A male subject, in their 40s. A dermoscopic view of a skin lesion.
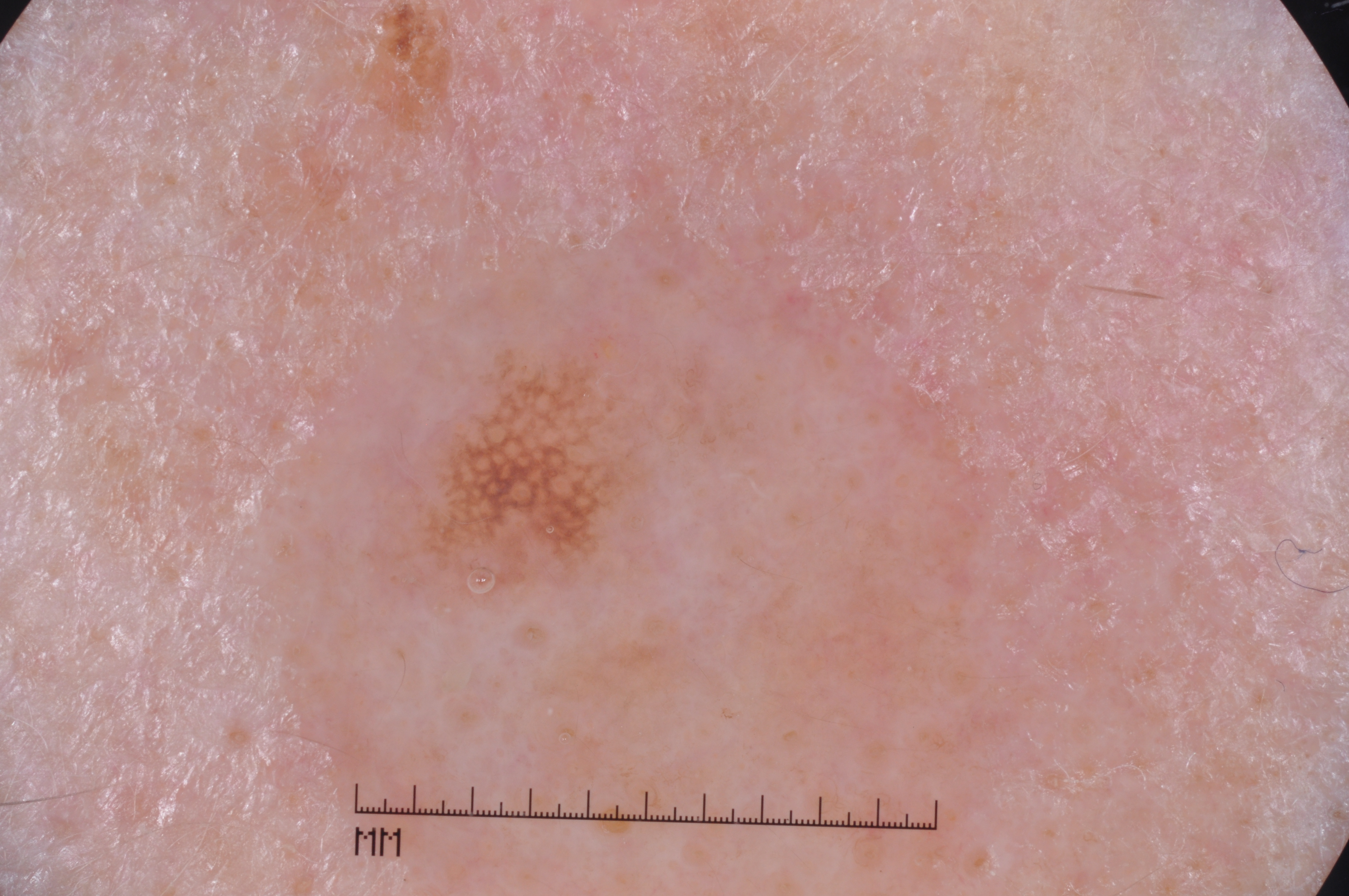Q: Which assessed dermoscopic features were absent?
A: milia-like cysts, pigment network, streaks, and negative network
Q: How large is the lesion within the image?
A: ~3% of the field
Q: What is the lesion's bounding box?
A: left=362, top=334, right=655, bottom=601
Q: What did the assessment conclude?
A: a seborrheic keratosis, a benign skin lesion